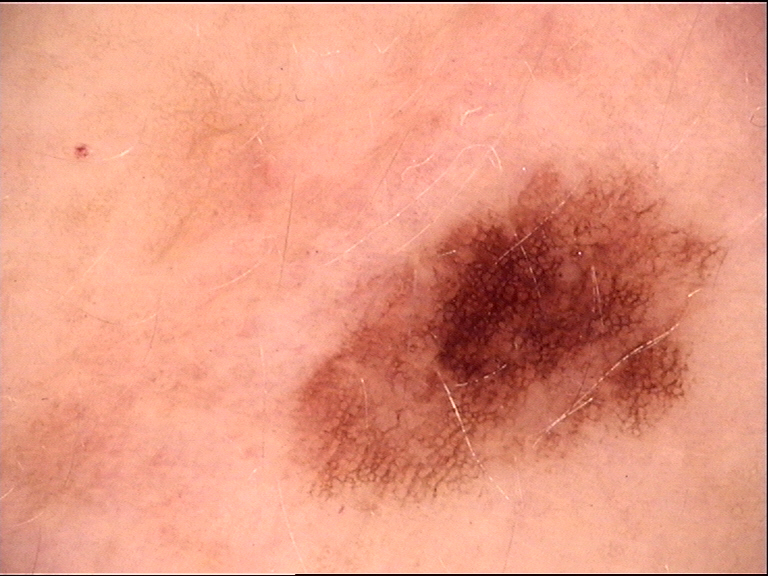image: dermatoscopy
diagnosis:
  name: dysplastic junctional nevus
  code: jd
  malignancy: benign
  super_class: melanocytic
  confirmation: expert consensus